A close-up photograph:
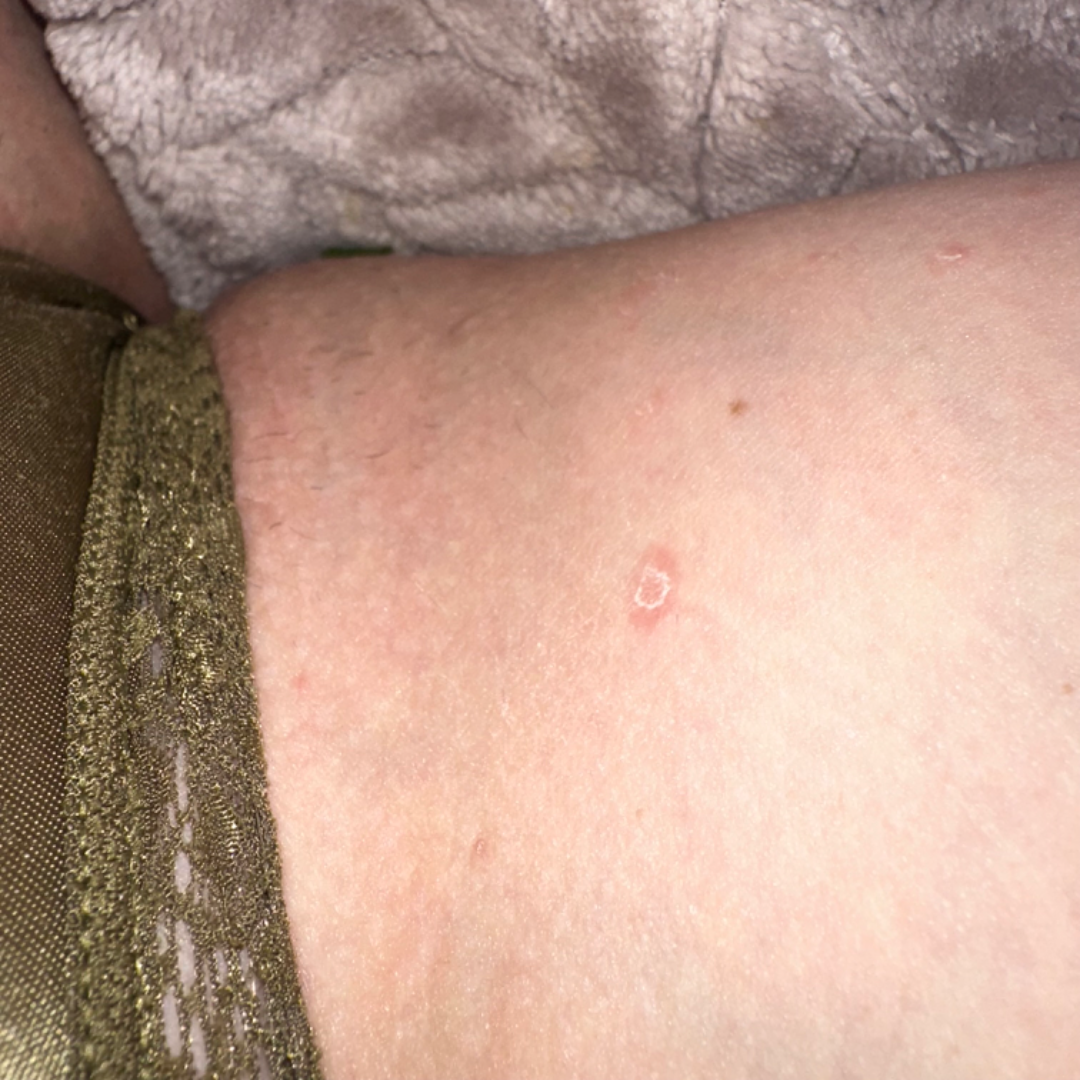Background:
Reported duration is one to four weeks. Symptoms reported: bothersome appearance, enlargement and itching. The patient considered this a rash. Texture is reported as flat and rough or flaky.
Findings:
On dermatologist assessment of the image: Pityriasis rosea (0.67); Psoriasis (0.33).